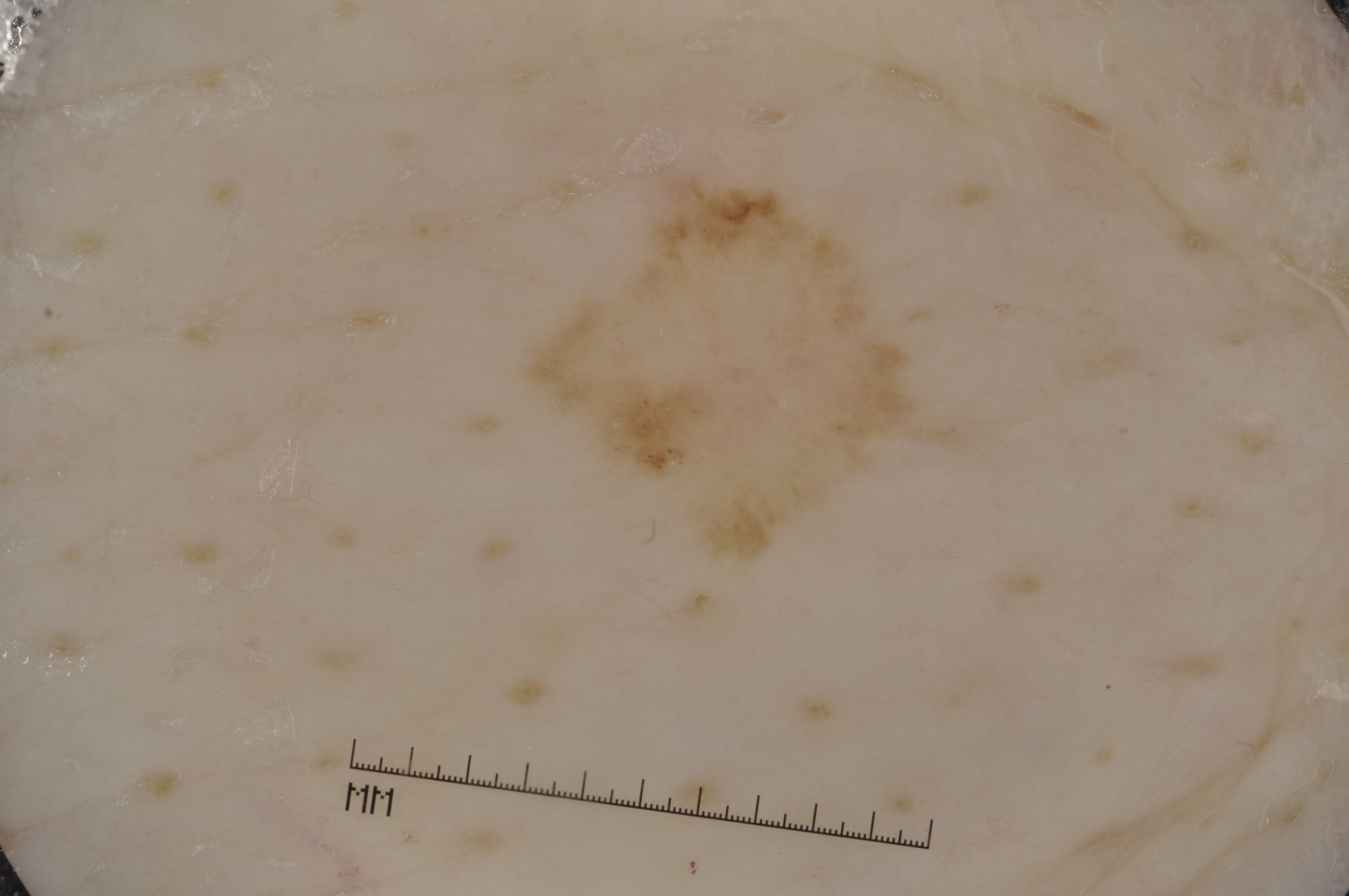imaging: dermoscopic image
subject: male, aged 83 or over
lesion bbox: <bbox>514, 159, 975, 582</bbox>
dermoscopic findings: milia-like cysts
impression: a seborrheic keratosis